A dermoscopic close-up of a skin lesion — 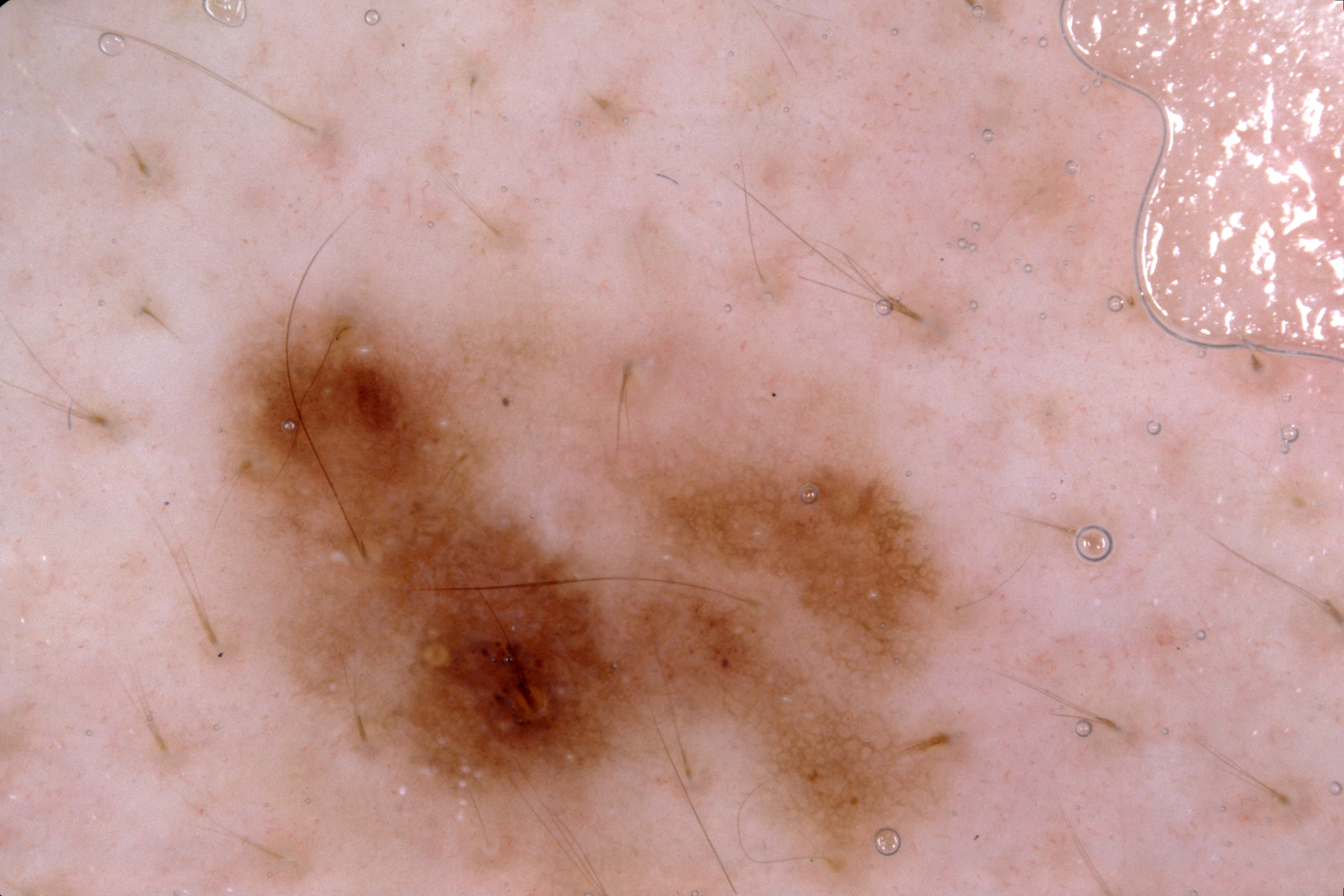  dermoscopic_features:
    present:
      - pigment network
      - milia-like cysts
    absent:
      - negative network
      - streaks
  lesion_location:
    bbox_xyxy:
      - 231
      - 301
      - 966
      - 826
  lesion_extent: moderate
  diagnosis:
    name: melanocytic nevus
    malignancy: benign
    lineage: melanocytic
    provenance: clinical